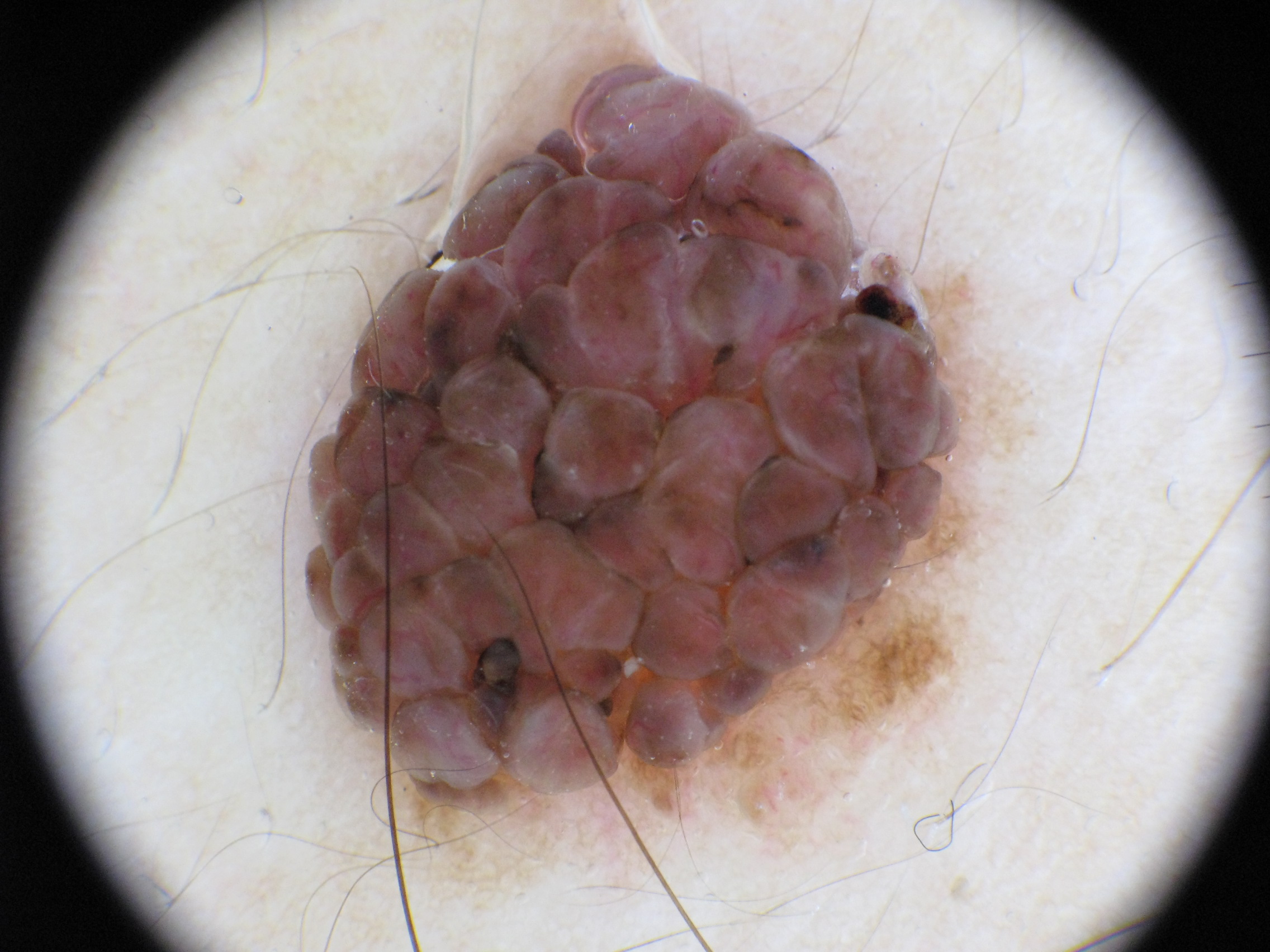{"image": {"modality": "dermoscopy"}, "dermoscopic_features": {"present": ["pigment network"], "absent": ["streaks", "globules", "milia-like cysts", "negative network"]}, "lesion_location": {"bbox_xyxy": [300, 56, 1048, 913]}, "diagnosis": {"name": "melanocytic nevus", "malignancy": "benign", "lineage": "melanocytic", "provenance": "clinical"}}